A dermoscopic close-up of a skin lesion · a male subject, about 30 years old.
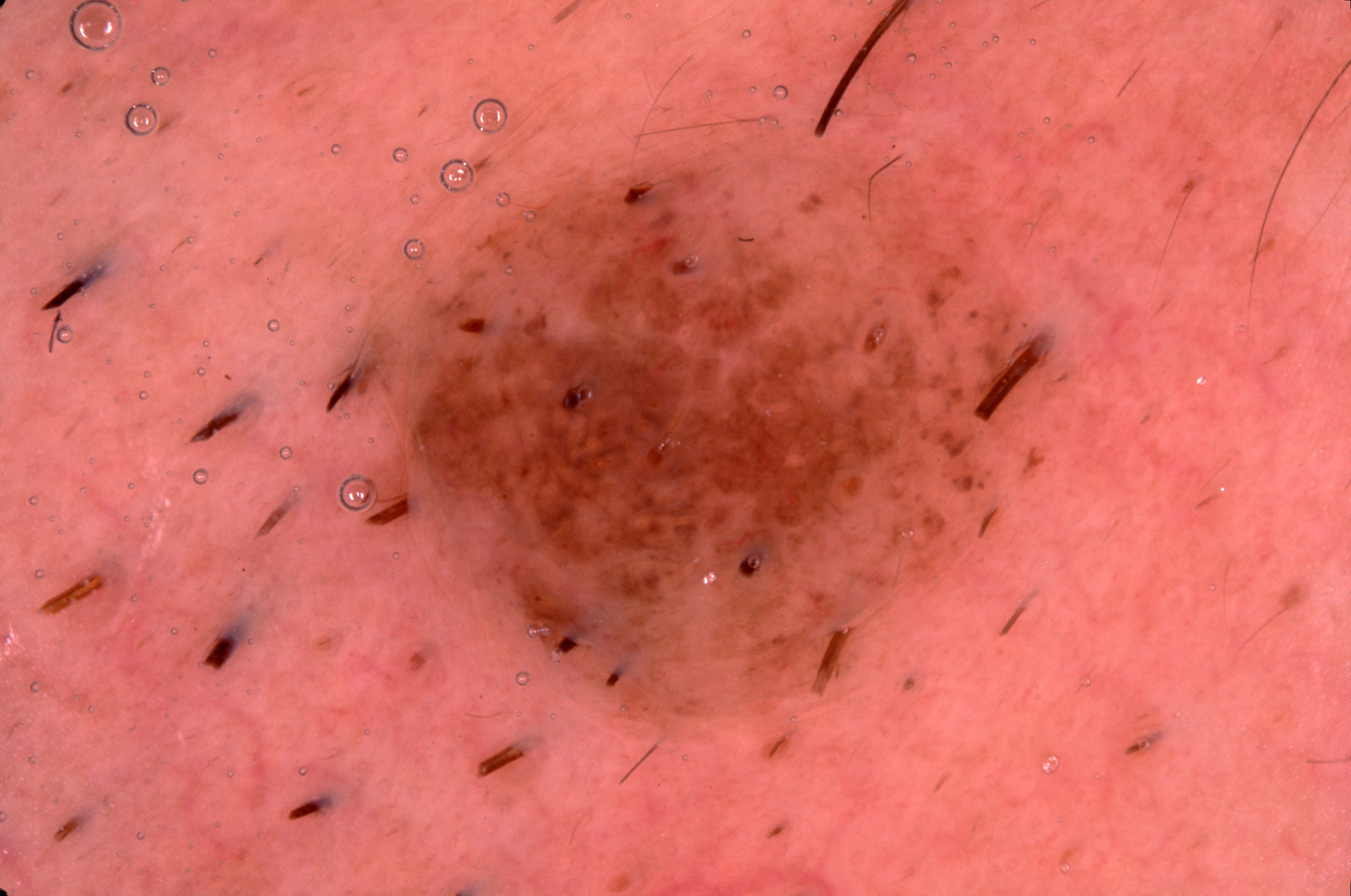Image and clinical context:
In (x1, y1, x2, y2) order, the lesion is located at 348, 161, 1045, 714. Dermoscopic examination shows no negative network, milia-like cysts, streaks, or pigment network.
Impression:
The lesion was assessed as a melanocytic nevus.